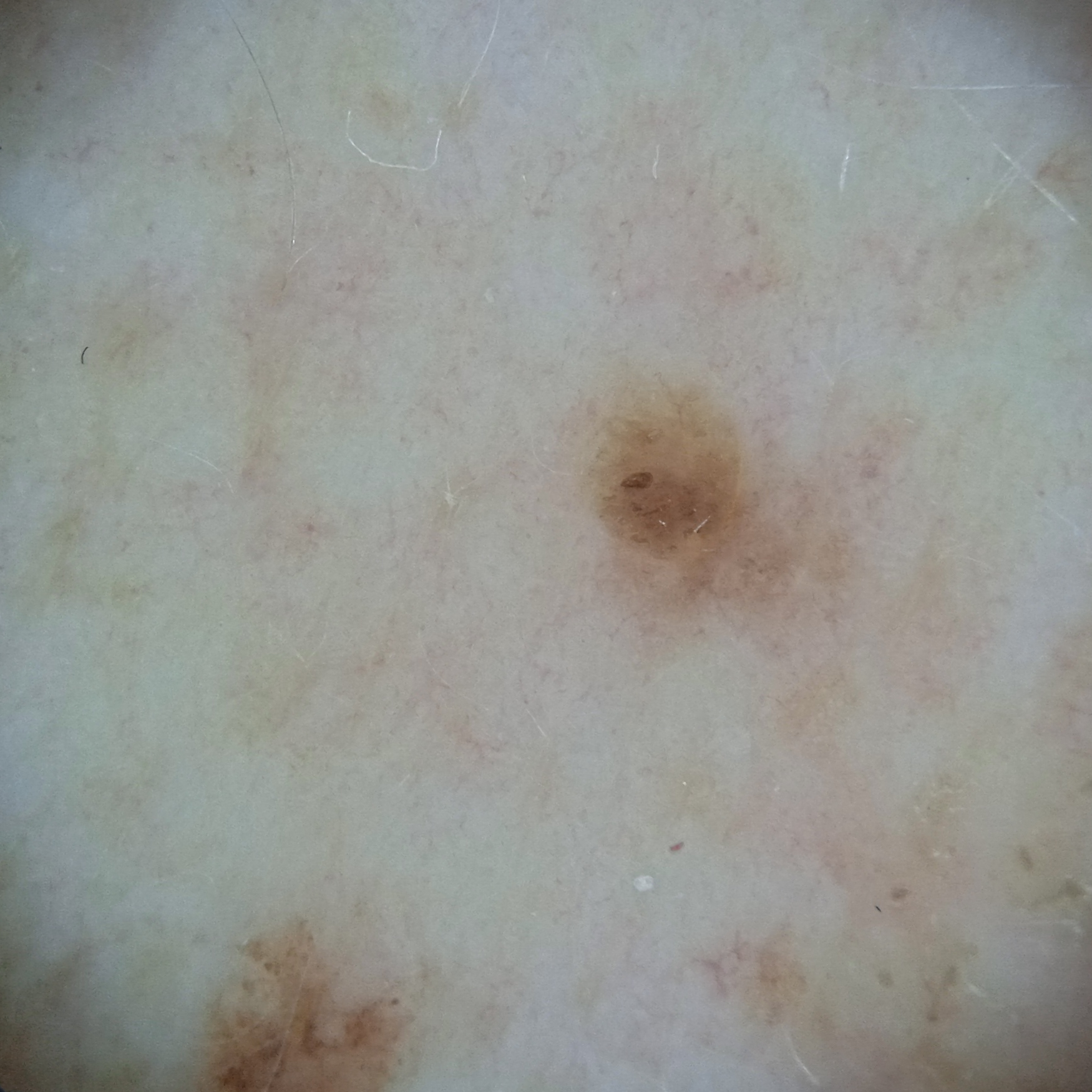<lesion>
<sun_reaction>skin reddens with sun exposure</sun_reaction>
<referral>research study (no referral diagnosis)</referral>
<patient>
<age>78</age>
<sex>male</sex>
</patient>
<risk_factors>
<positive>a personal history of cancer</positive>
<negative>no immunosuppression</negative>
</risk_factors>
<image>dermoscopic image</image>
<mole_burden>few melanocytic nevi overall</mole_burden>
<lesion_location>the back</lesion_location>
<lesion_size>
<diameter_mm>3.1</diameter_mm>
</lesion_size>
<diagnosis>
<name>seborrheic keratosis</name>
<malignancy>benign</malignancy>
<unanimous>false</unanimous>
<certainty>moderate</certainty>
</diagnosis>
</lesion>